Dermoscopy of a skin lesion; the patient says their skin reddens painfully with sun exposure; by self-report, a history of sunbed use and a family history of skin cancer; acquired for a research image collection, with no referral diagnosis; a female subject 48 years old; few moles overall by the patient's own estimate: 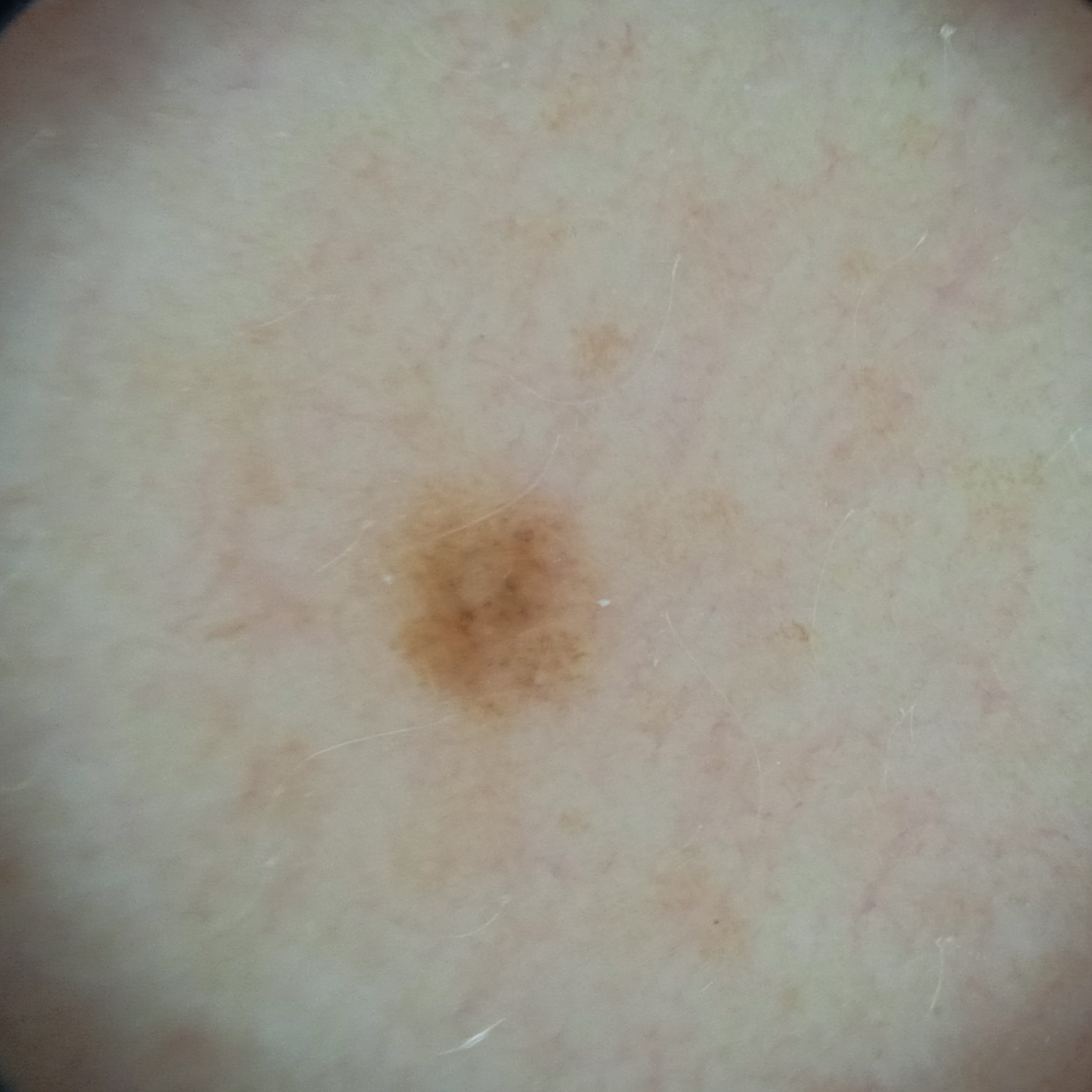The lesion is on an arm. Measuring roughly 2.7 mm. The consensus diagnosis for this lesion was a melanocytic nevus.